A dermoscopic photograph of a skin lesion.
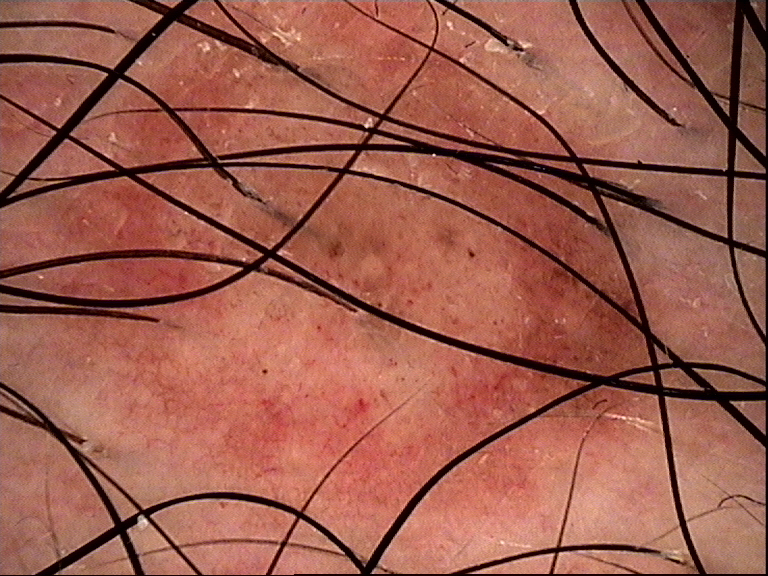Consistent with a banal lesion — a dermal nevus.